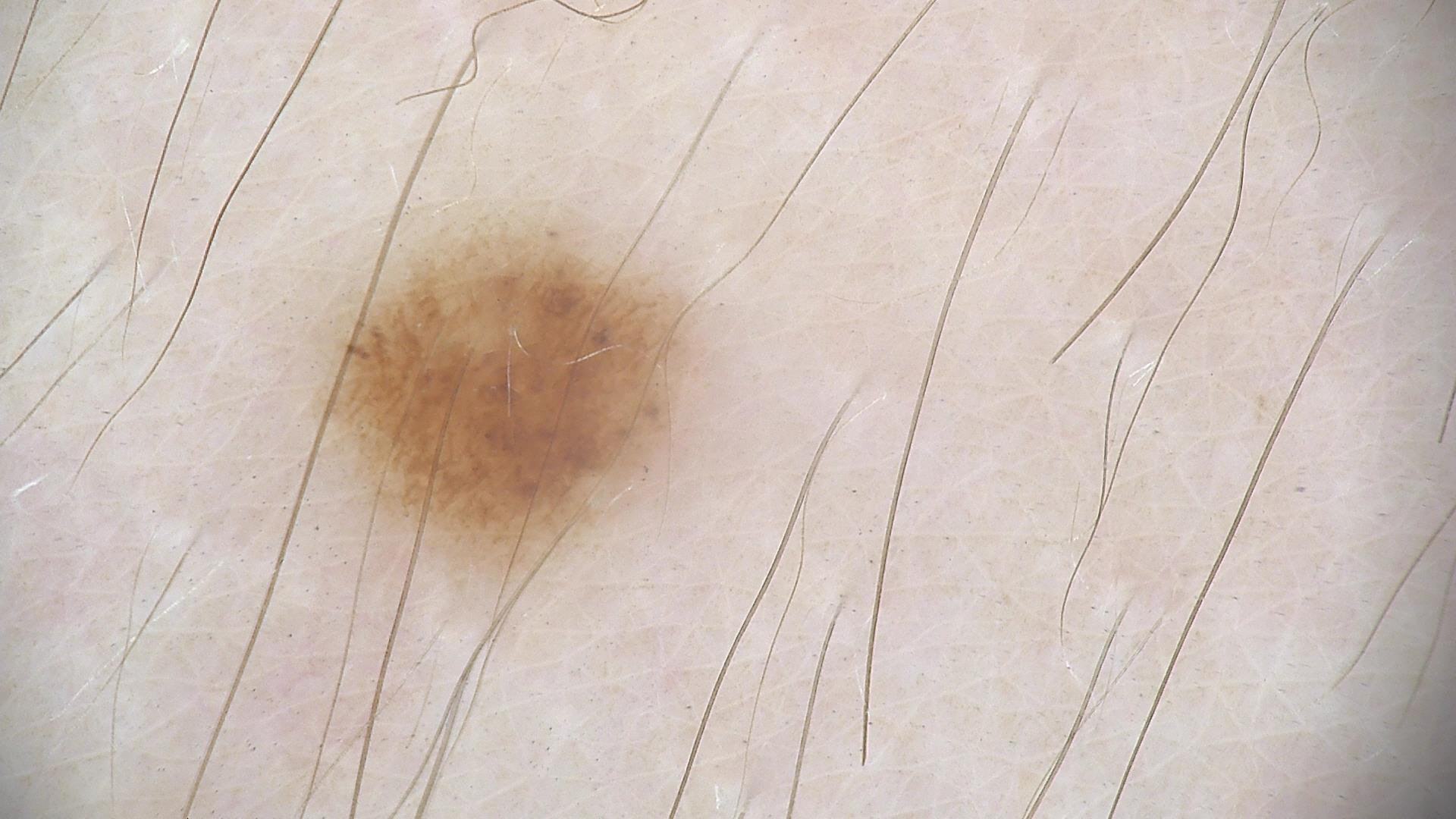Conclusion: Diagnosed as a dysplastic junctional nevus.